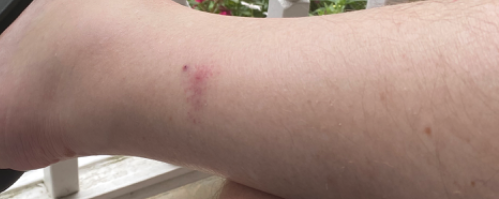On teledermatology review, Allergic Contact Dermatitis (leading); Insect Bite (considered); Eczema (considered).